A female subject about 45 years old, dermoscopy of a skin lesion: 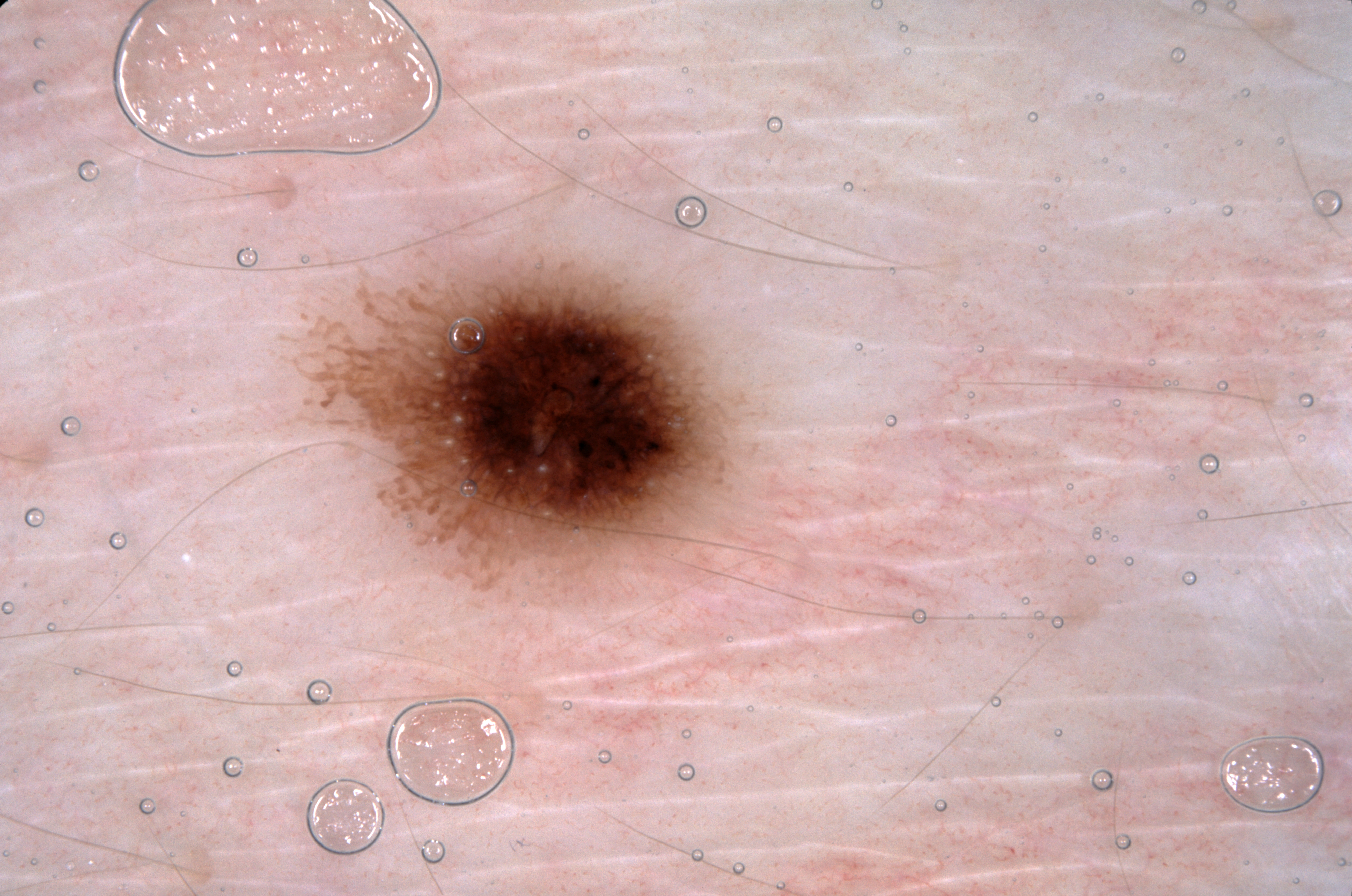Image and clinical context: Dermoscopic examination shows milia-like cysts and pigment network; no negative network or streaks. The lesion's extent is left=290, top=242, right=794, bottom=610. The lesion covers approximately 10% of the dermoscopic field. Assessment: Clinically diagnosed as a melanocytic nevus, a benign lesion.